The patient is female. Fitzpatrick IV; non-clinician graders estimated 3 on the MST. Reported lesion symptoms include bothersome appearance. The lesion involves the arm and leg. Texture is reported as raised or bumpy and rough or flaky. An image taken at an angle: 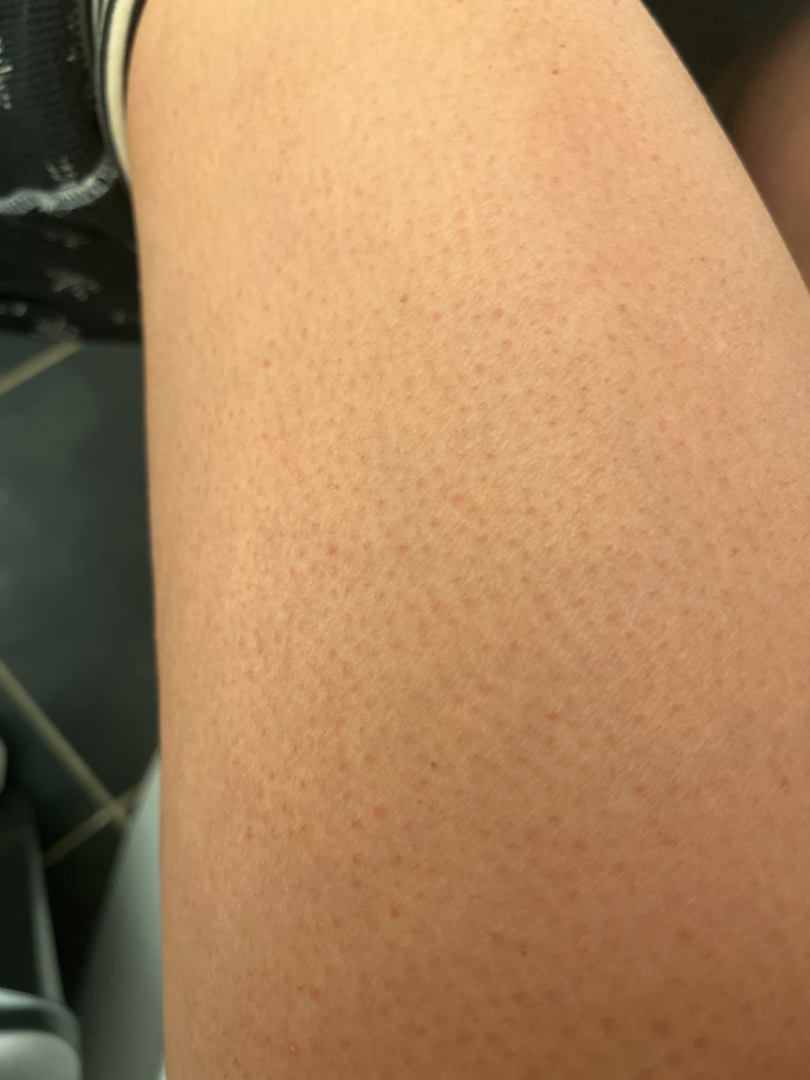On remote dermatologist review, consistent with Keratosis pilaris.